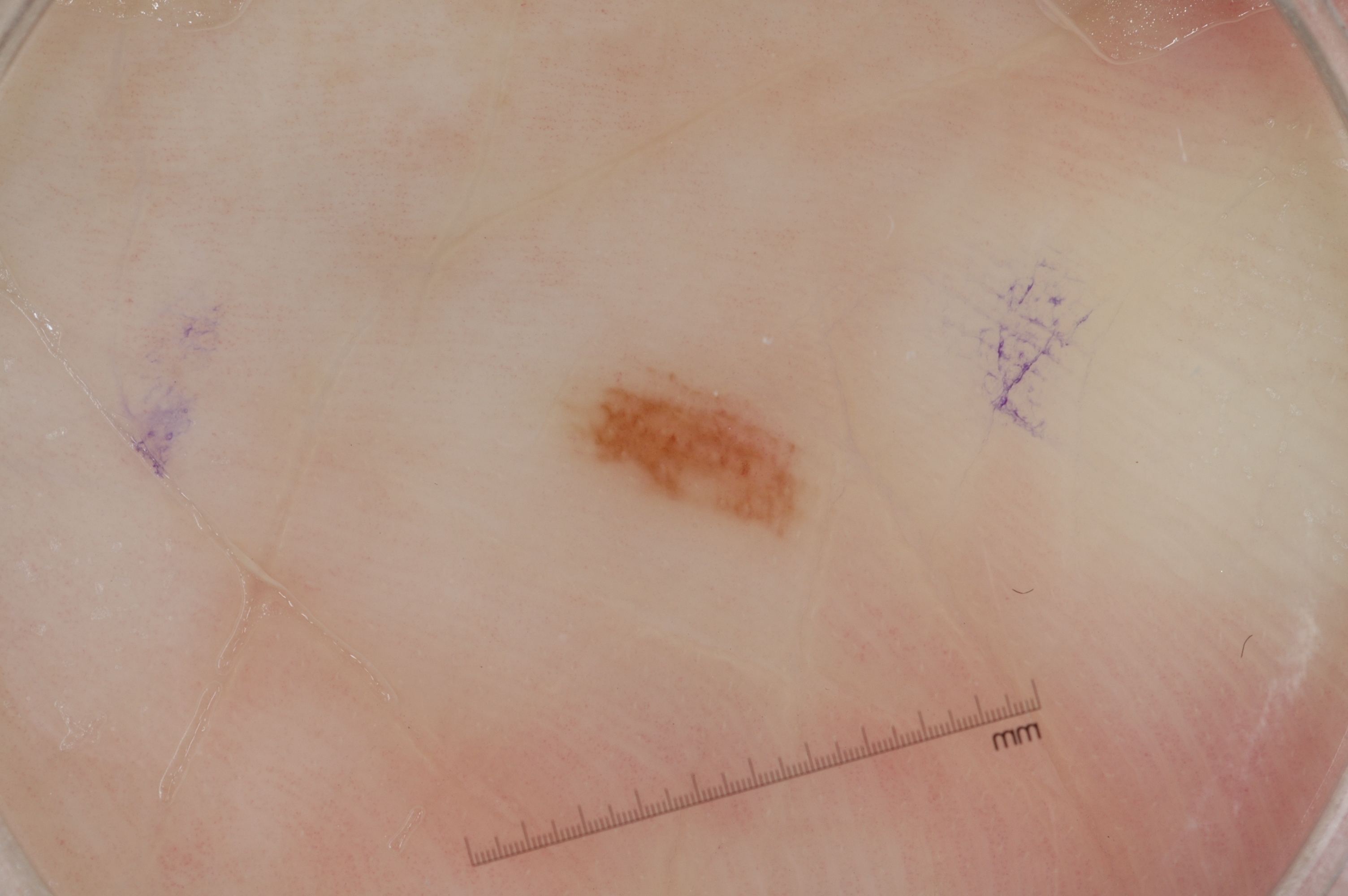Q: What kind of image is this?
A: dermoscopic image
Q: Patient demographics?
A: female, aged approximately 60
Q: Which assessed dermoscopic features were absent?
A: negative network, pigment network, milia-like cysts, and streaks
Q: How much of the field does the lesion occupy?
A: ~3% of the field
Q: Where is the lesion in the image?
A: <bbox>558, 364, 810, 538</bbox>
Q: What did the assessment conclude?
A: a melanocytic nevus, a benign lesion